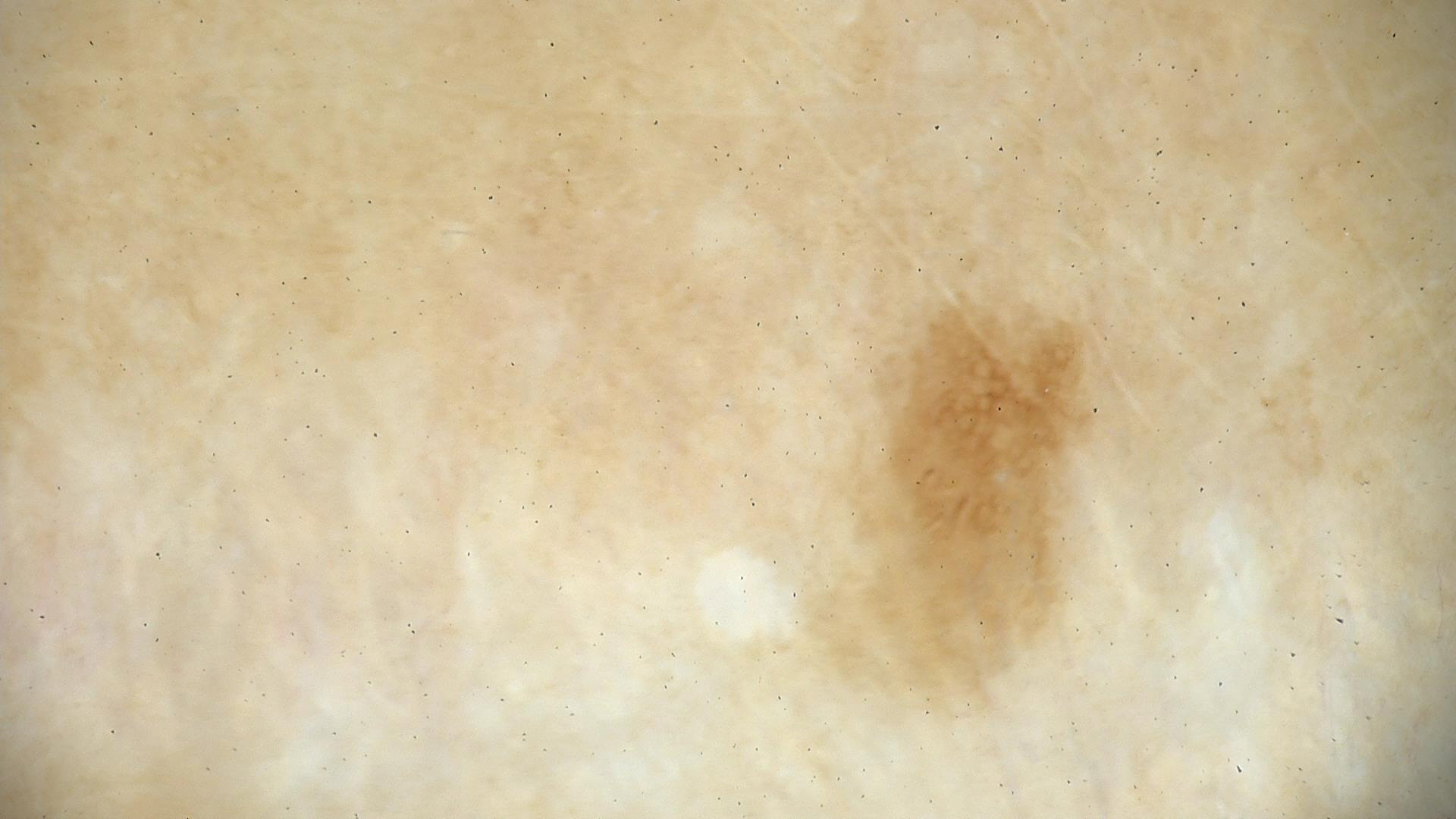Conclusion: Diagnosed as a recurrent nevus.